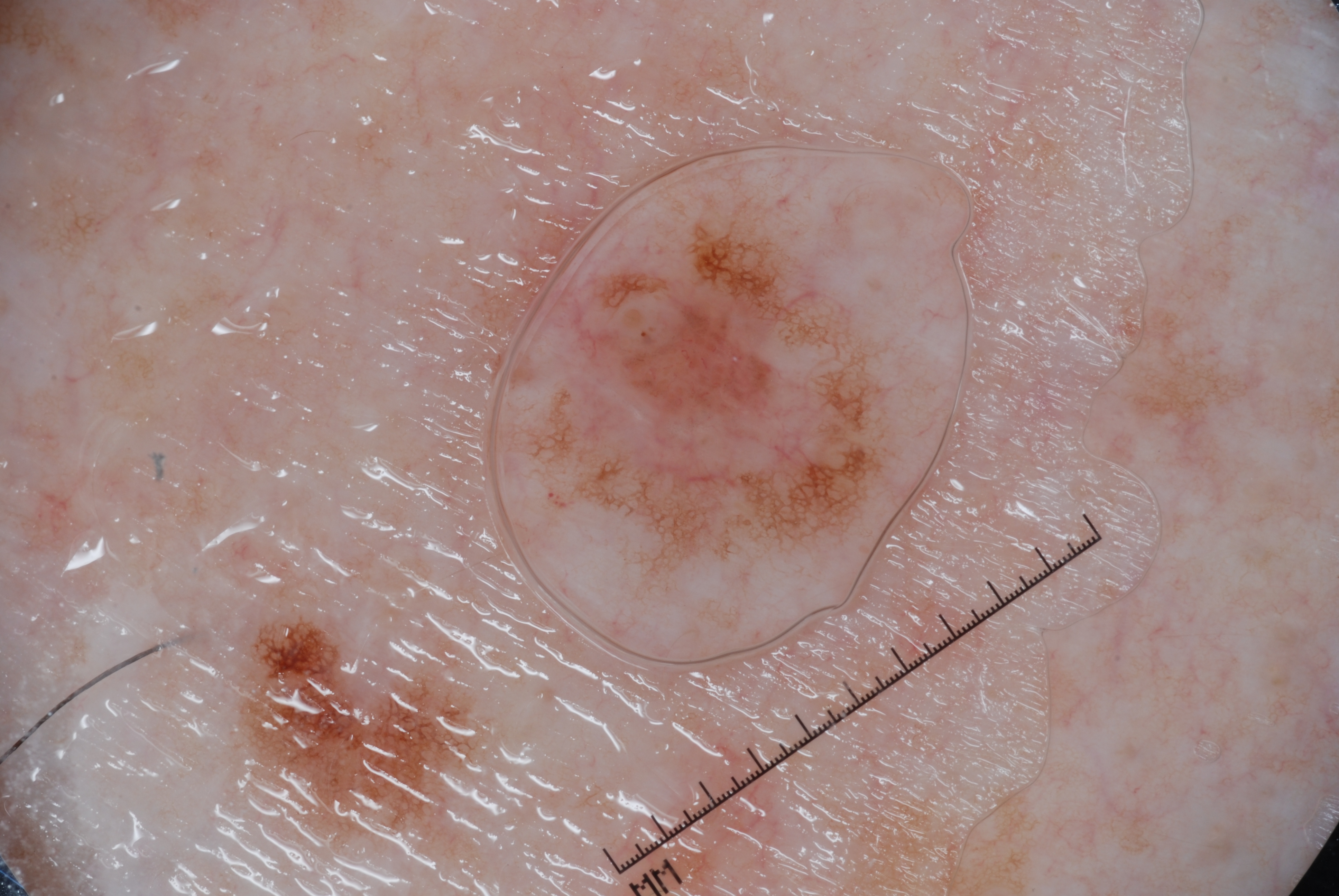Notes:
• modality: dermoscopy
• subject: male, aged approximately 40
• dermoscopic features: pigment network and milia-like cysts
• lesion bbox: x1=544 y1=217 x2=889 y2=553
• diagnosis: a melanocytic nevus, a benign lesion